A dermoscopic close-up of a skin lesion.
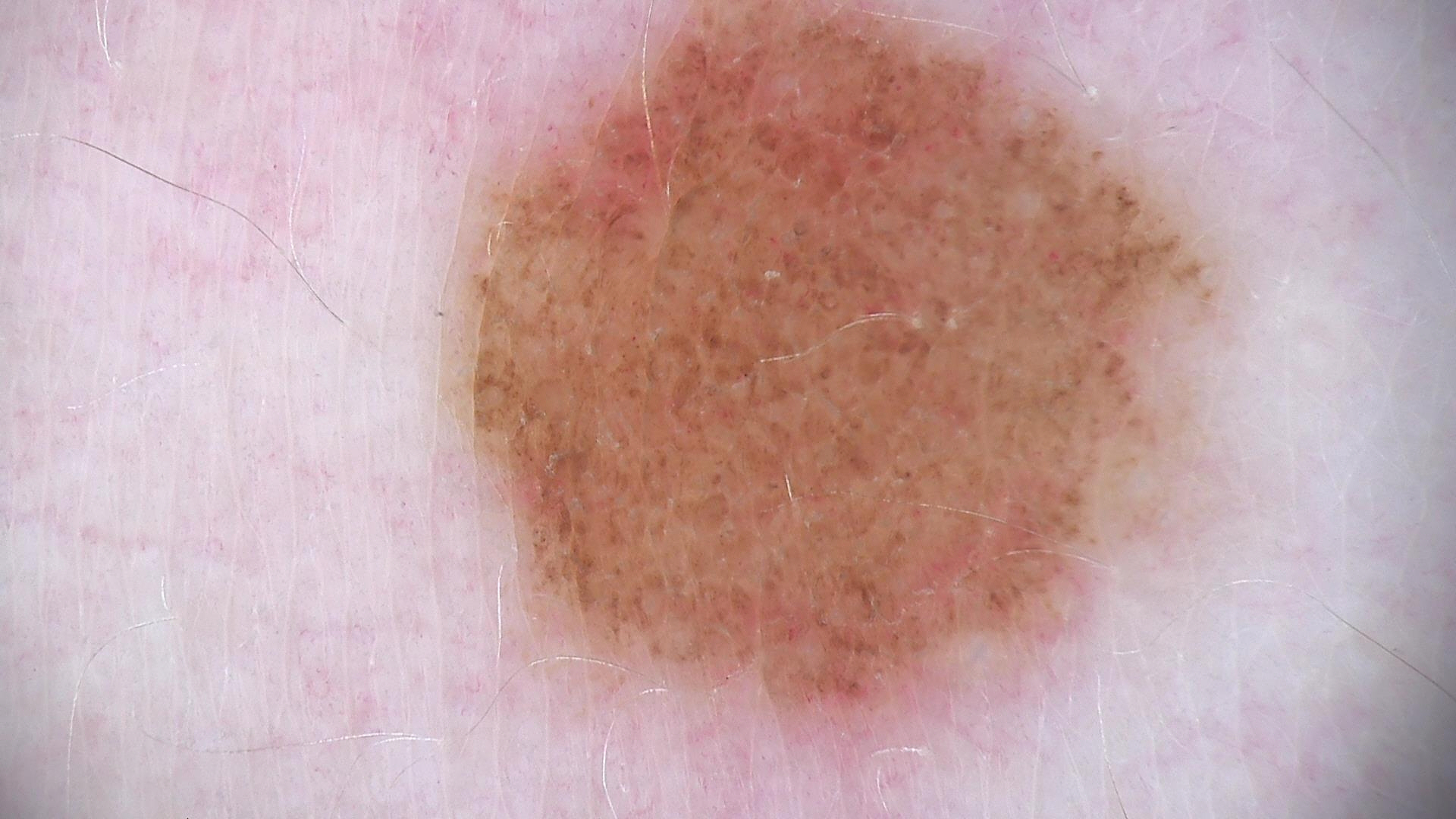The diagnostic label was a banal lesion — a congenital compound nevus.